A male patient; a dermoscopic close-up of a skin lesion — 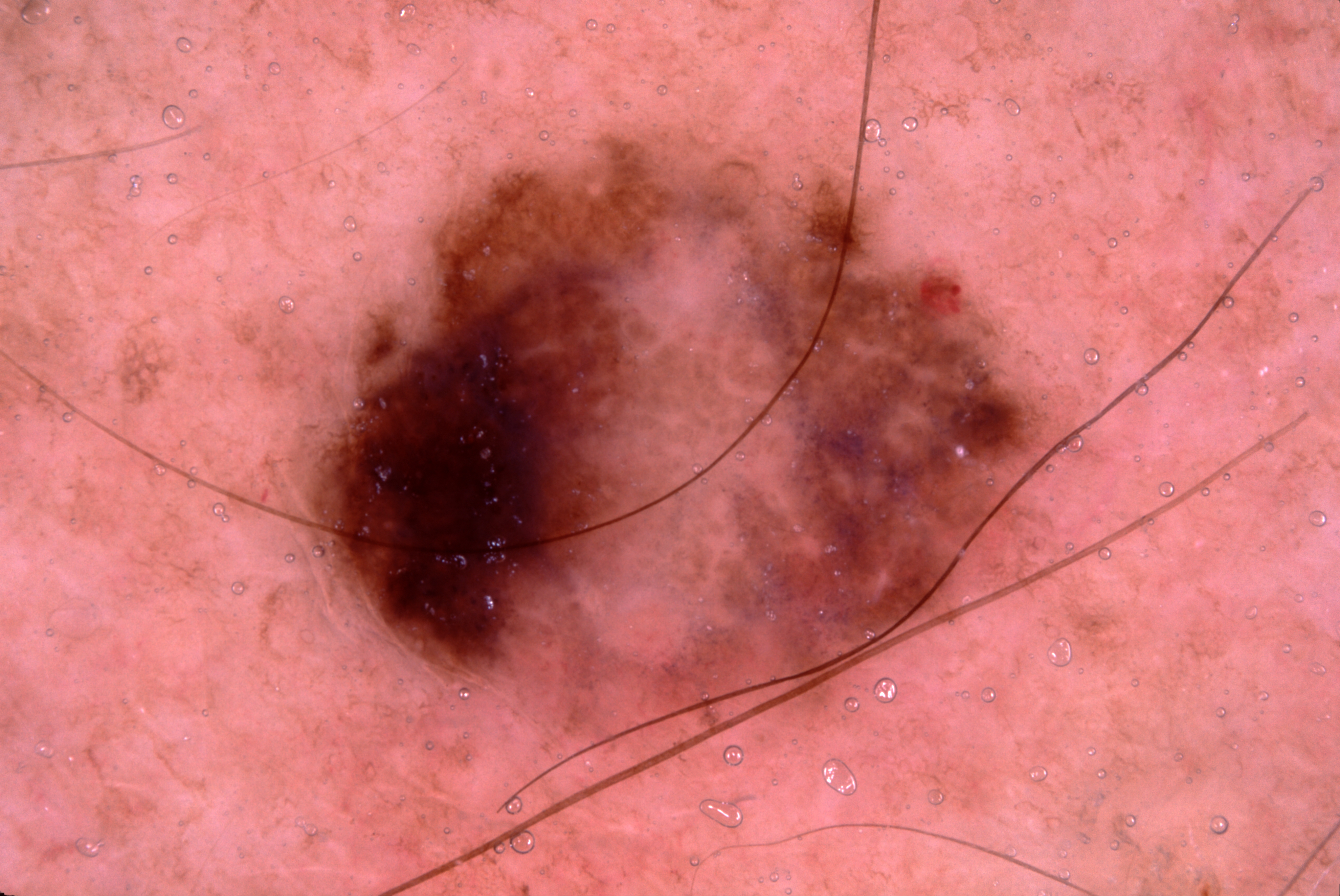Dermoscopy demonstrates negative network and pigment network.
The lesion spans 304, 133, 1057, 749.
The lesion covers approximately 27% of the dermoscopic field.
Histopathological examination showed a melanoma.